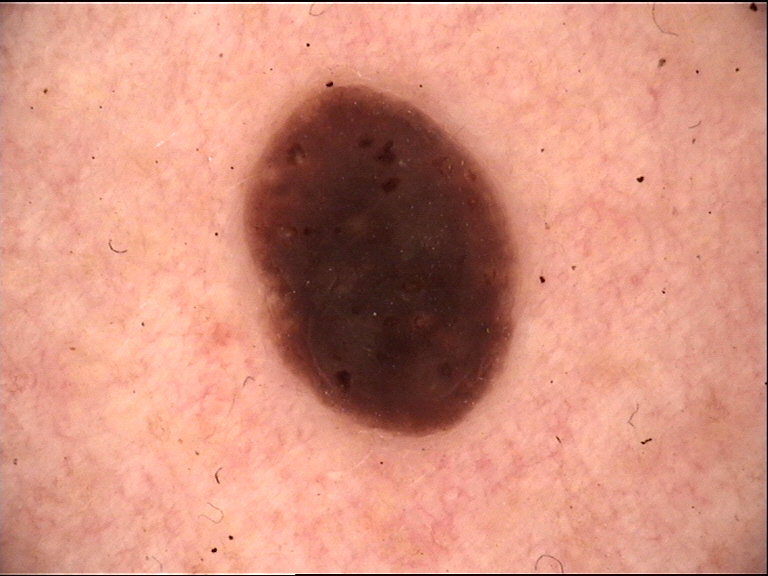Consistent with a seborrheic keratosis.